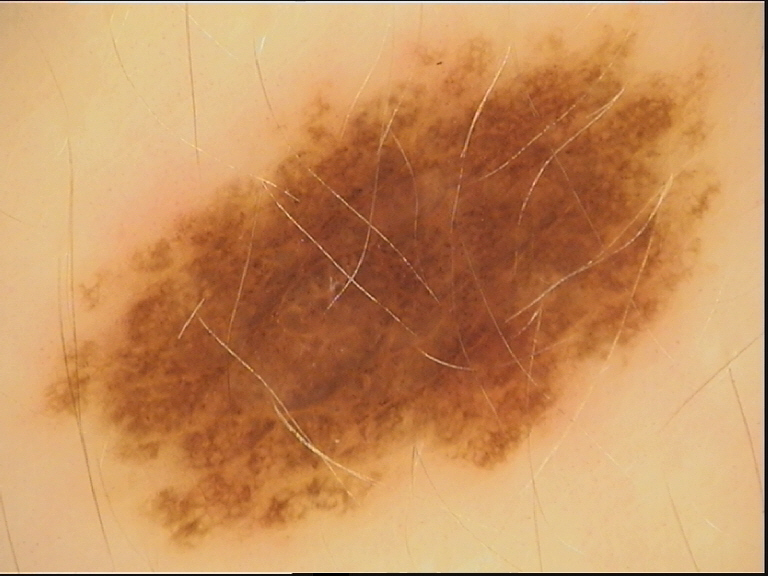A dermoscopic photograph of a skin lesion. The diagnostic label was a benign lesion — a dysplastic junctional nevus.